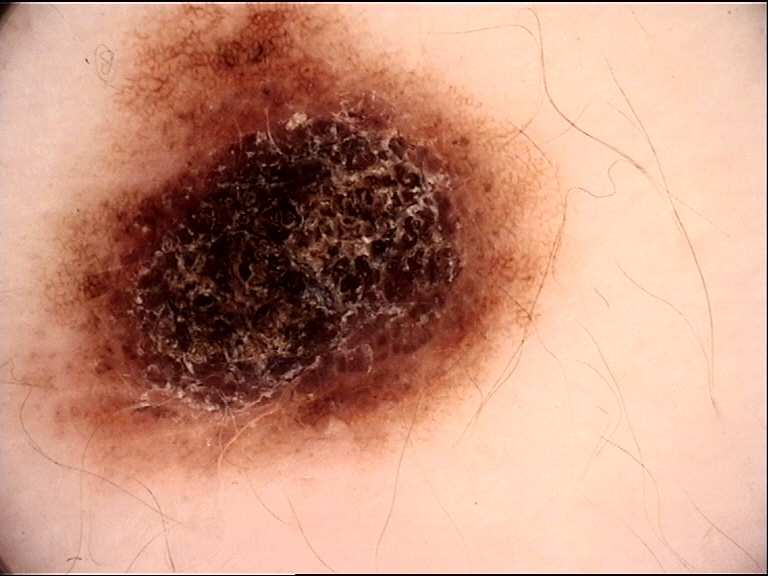Q: What was the diagnostic impression?
A: dysplastic compound nevus (expert consensus)